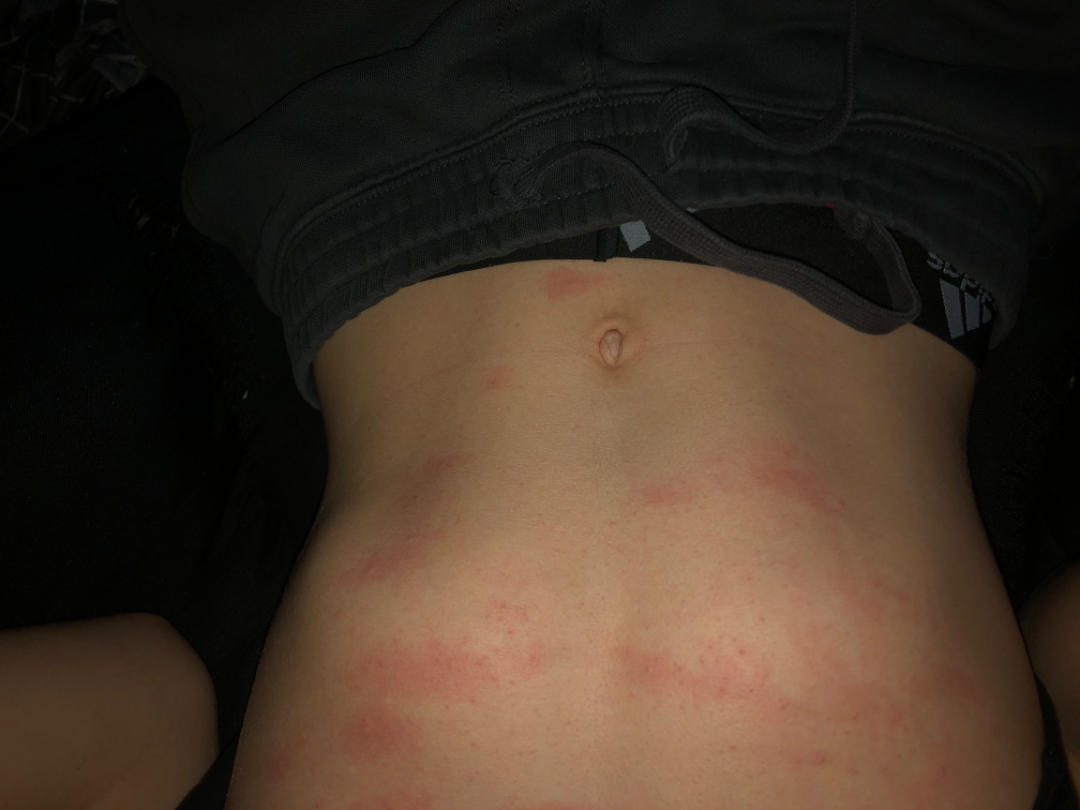patient = male, age 18–29; symptoms = itching; body site = front of the torso; framing = at a distance; diagnostic considerations = a single dermatologist reviewed the case: the differential, in no particular order, includes Urticaria and Eczema.